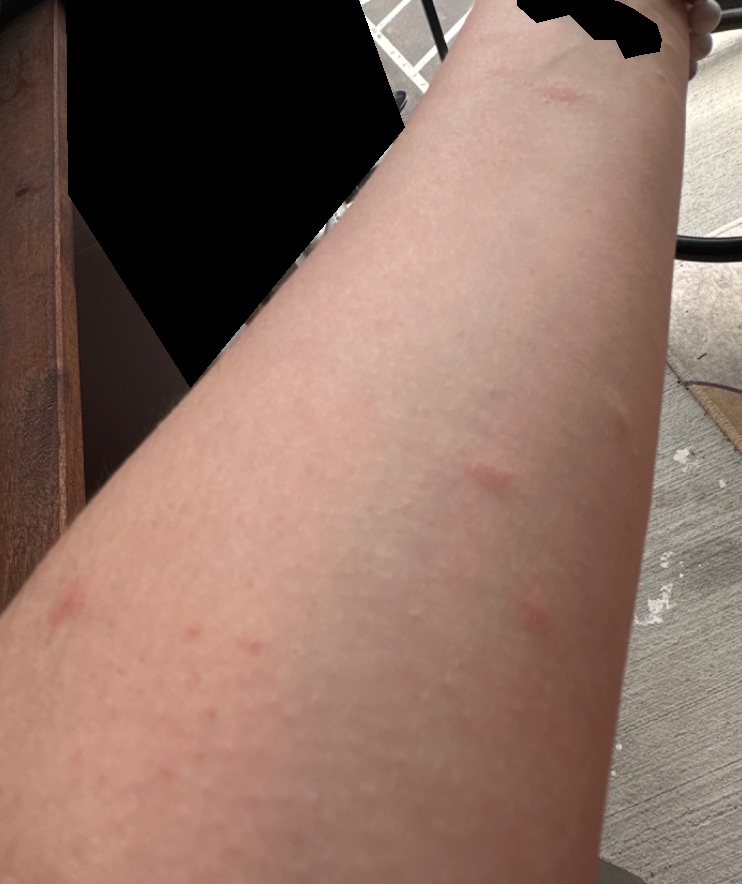Patient information: The affected area is the back of the torso, back of the hand, head or neck, arm, front of the torso and leg. The photograph was taken at an angle. The patient considered this a rash. Texture is reported as rough or flaky and raised or bumpy. Present for one to four weeks. The lesion is associated with itching and enlargement. Review: Eczema (100%).